A dermatoscopic image of a skin lesion.
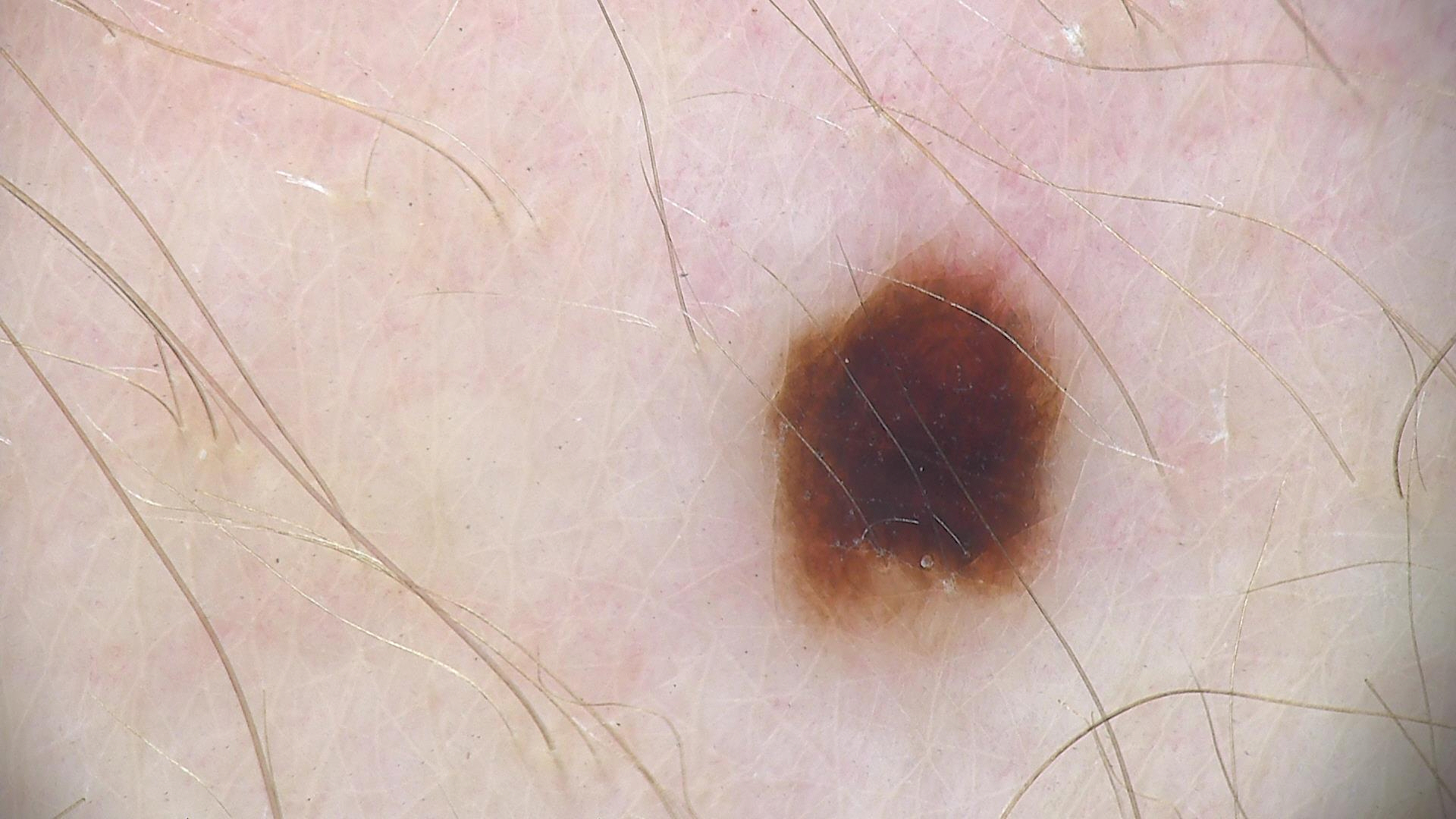Impression: Consistent with a benign lesion — a dysplastic junctional nevus.